A skin lesion imaged with a dermatoscope.
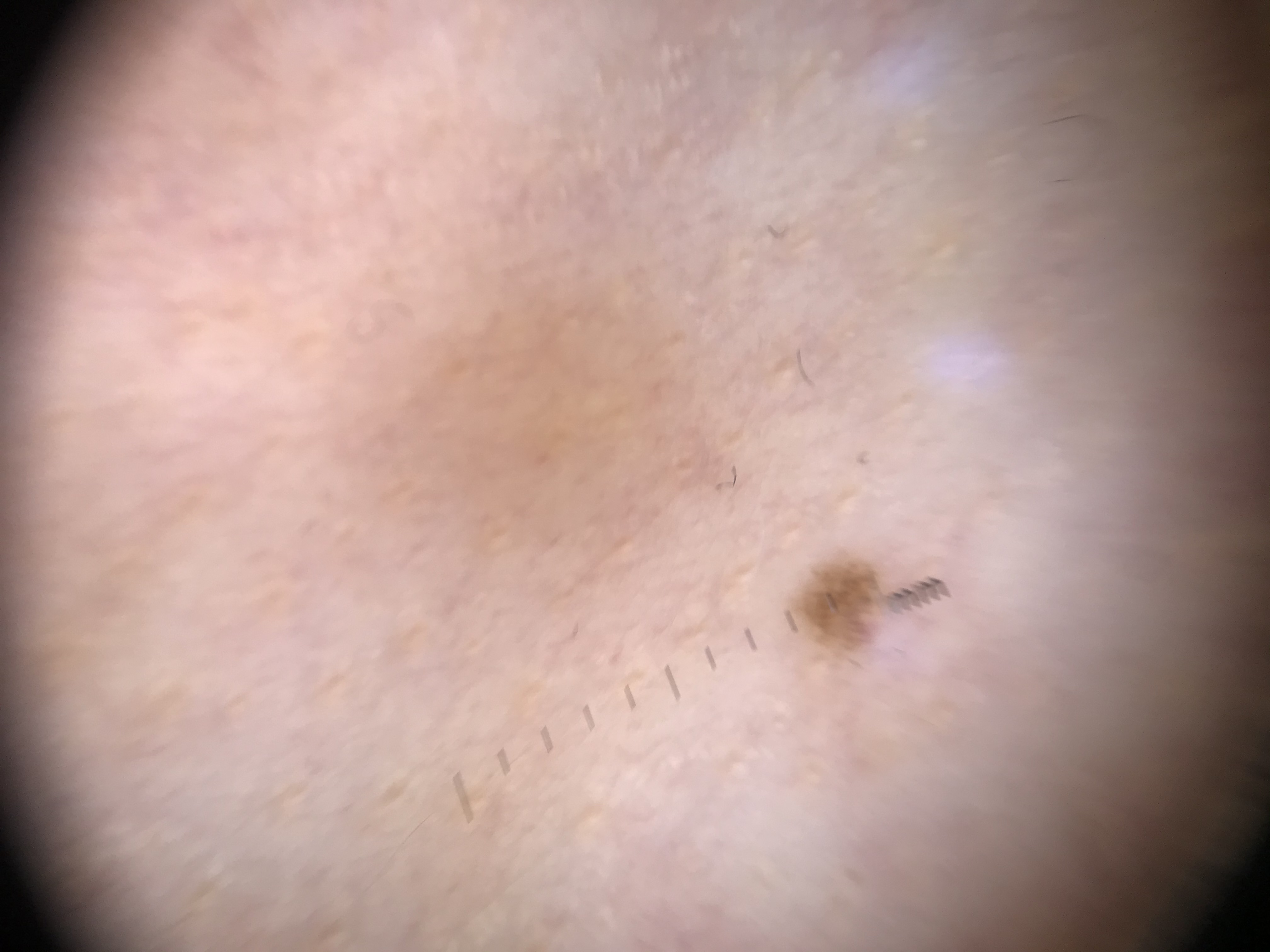Consistent with a junctional nevus.